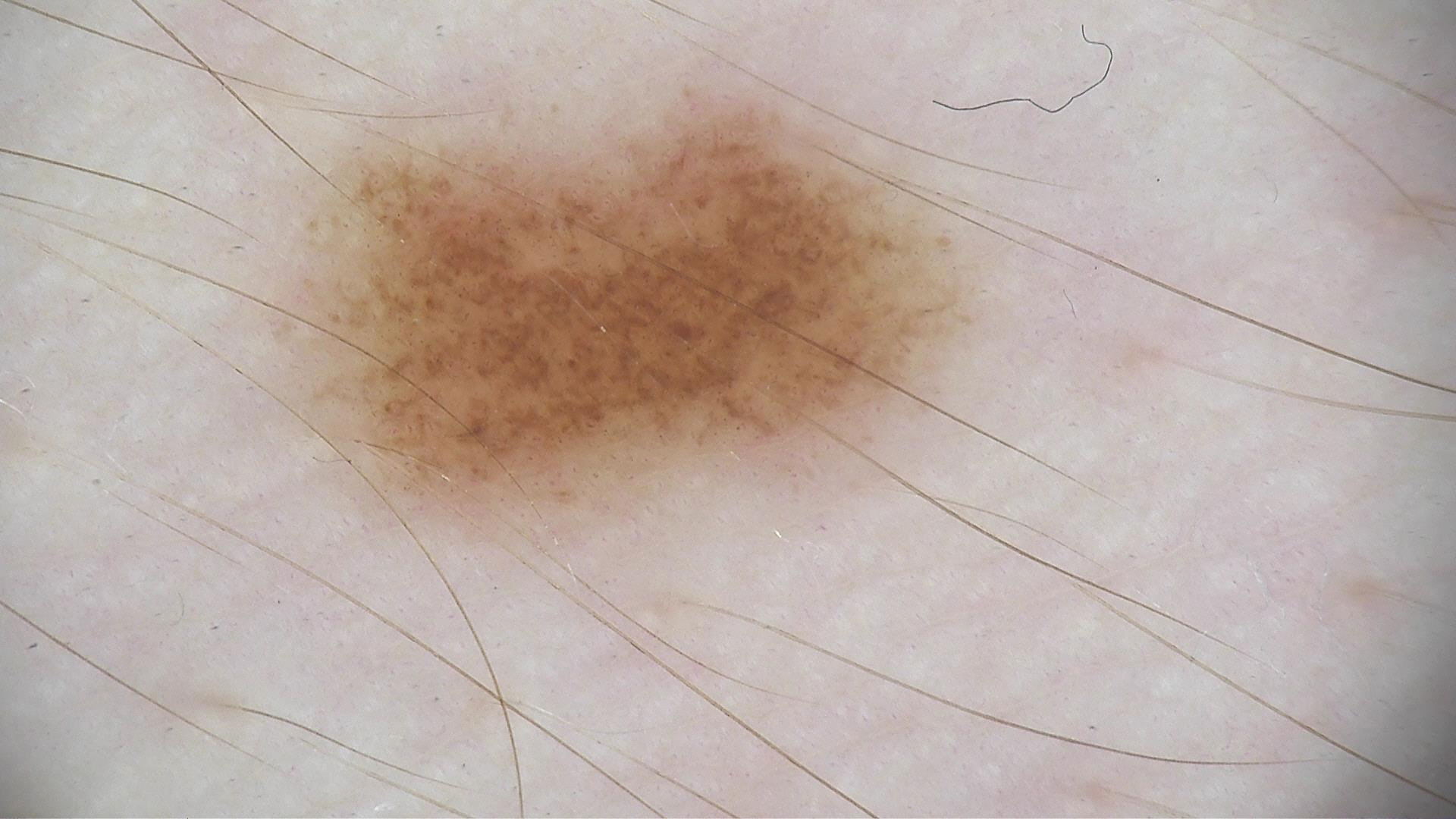Findings:
• label — dysplastic junctional nevus (expert consensus)